A skin lesion imaged with a dermatoscope:
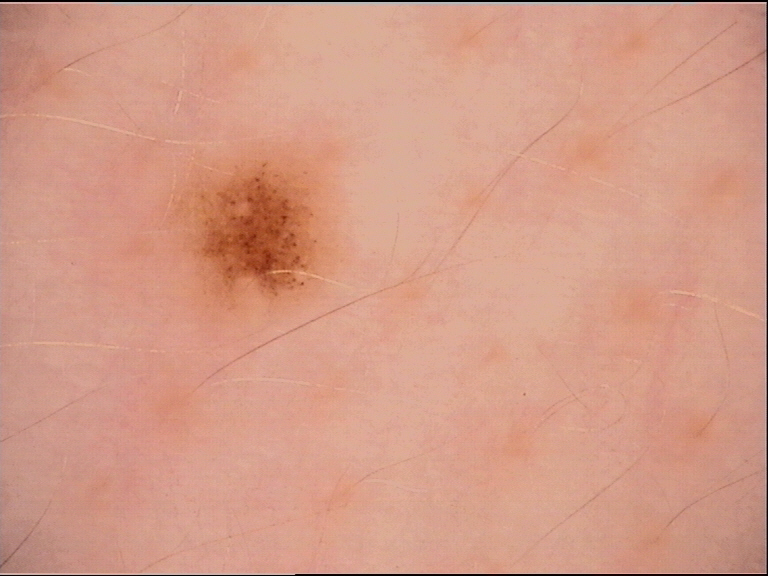Q: What was the diagnostic impression?
A: junctional nevus (expert consensus)